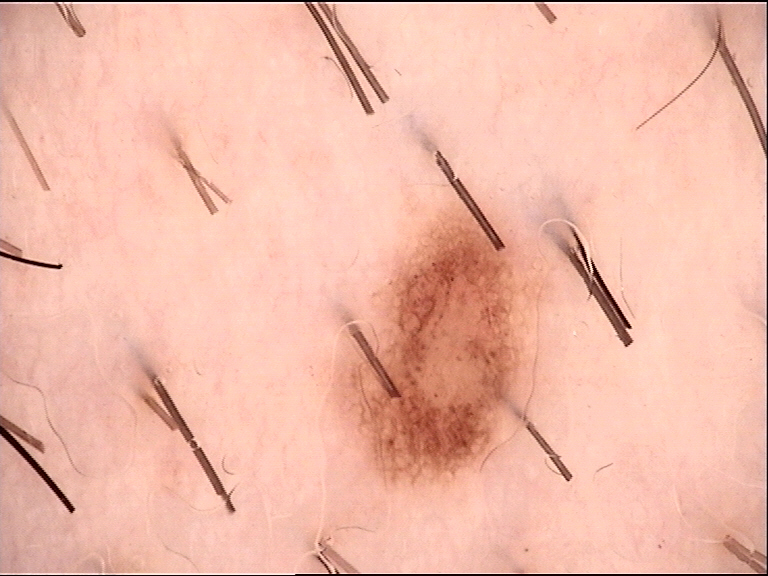Diagnosed as a dysplastic junctional nevus.